A dermoscopic photograph of a skin lesion: 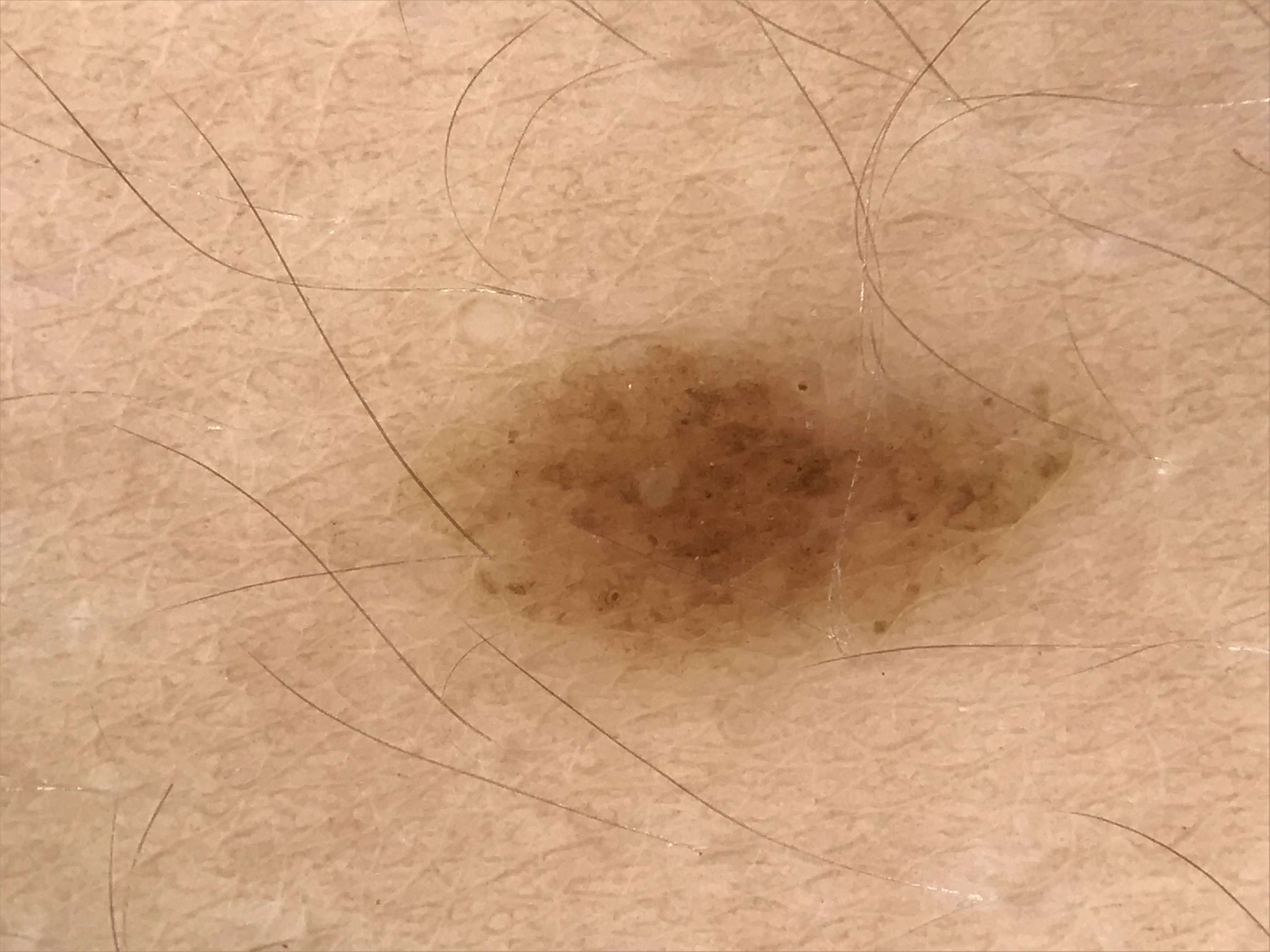The architecture is that of a banal lesion. Diagnosed as a junctional nevus.